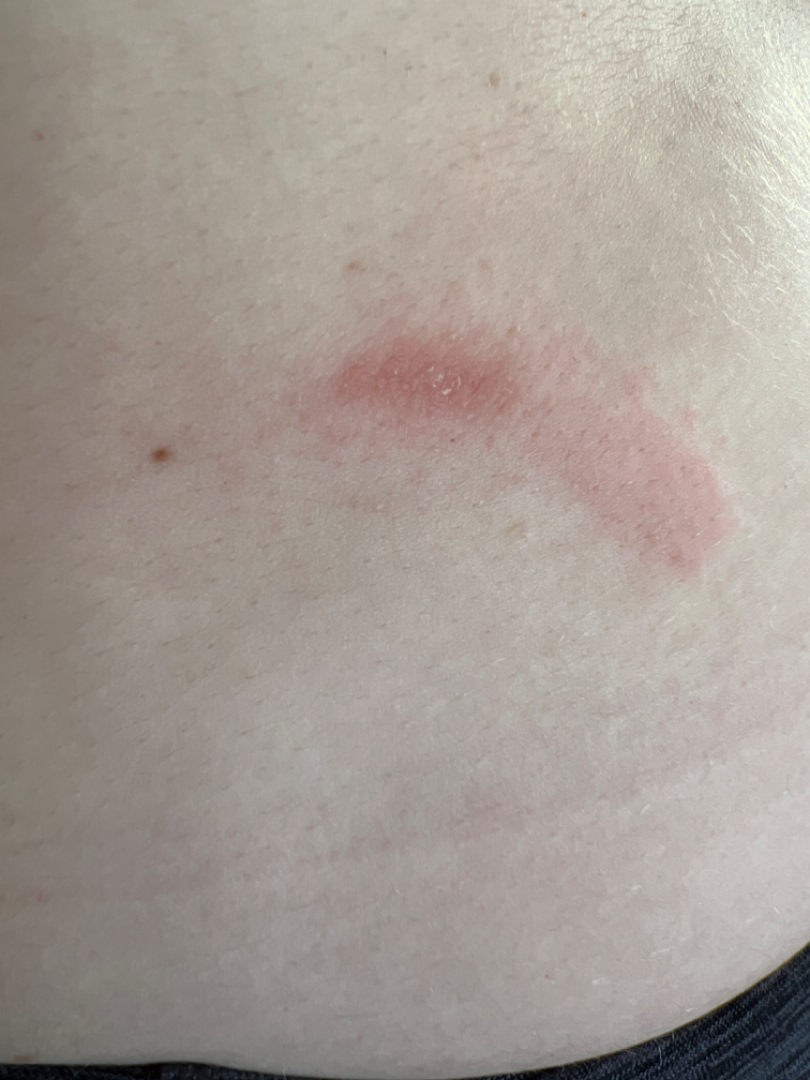<report>
<patient_category>a rash</patient_category>
<systemic_symptoms>none reported</systemic_symptoms>
<shot_type>at a distance</shot_type>
<body_site>front of the torso</body_site>
<texture>rough or flaky, raised or bumpy</texture>
<duration>one to four weeks</duration>
<symptoms>enlargement, itching</symptoms>
<patient>female, age 30–39</patient>
<differential>
  <leading>Allergic Contact Dermatitis</leading>
  <considered>Contact dermatitis</considered>
  <unlikely>Acute dermatitis, NOS; Irritant Contact Dermatitis; Urticaria</unlikely>
</differential>
</report>